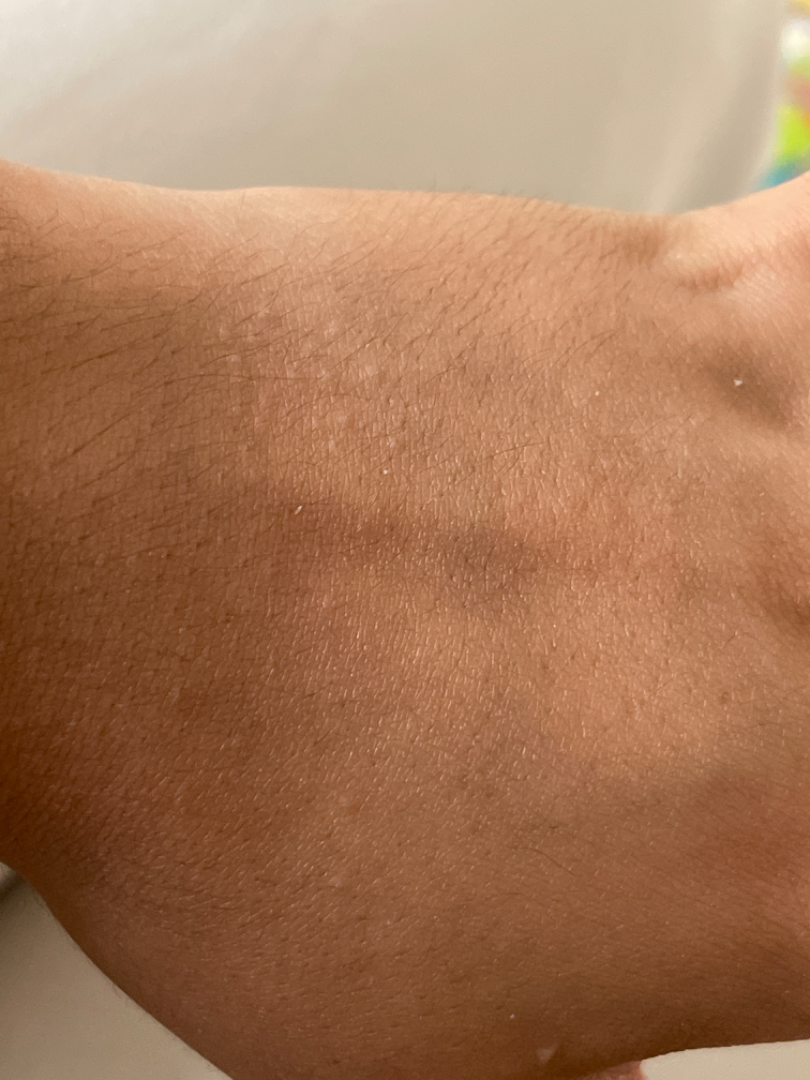assessment: indeterminate
shot_type: close-up
patient_category: a rash
duration: less than one week
systemic_symptoms: none reported
symptoms: none reported
body_site: back of the hand
texture: raised or bumpy